Located on the leg · the patient notes enlargement, pain, bothersome appearance and itching · self-categorized by the patient as a rash · a close-up photograph · FST IV · the lesion is described as raised or bumpy · female subject, age 40–49 · associated systemic symptoms include fatigue:
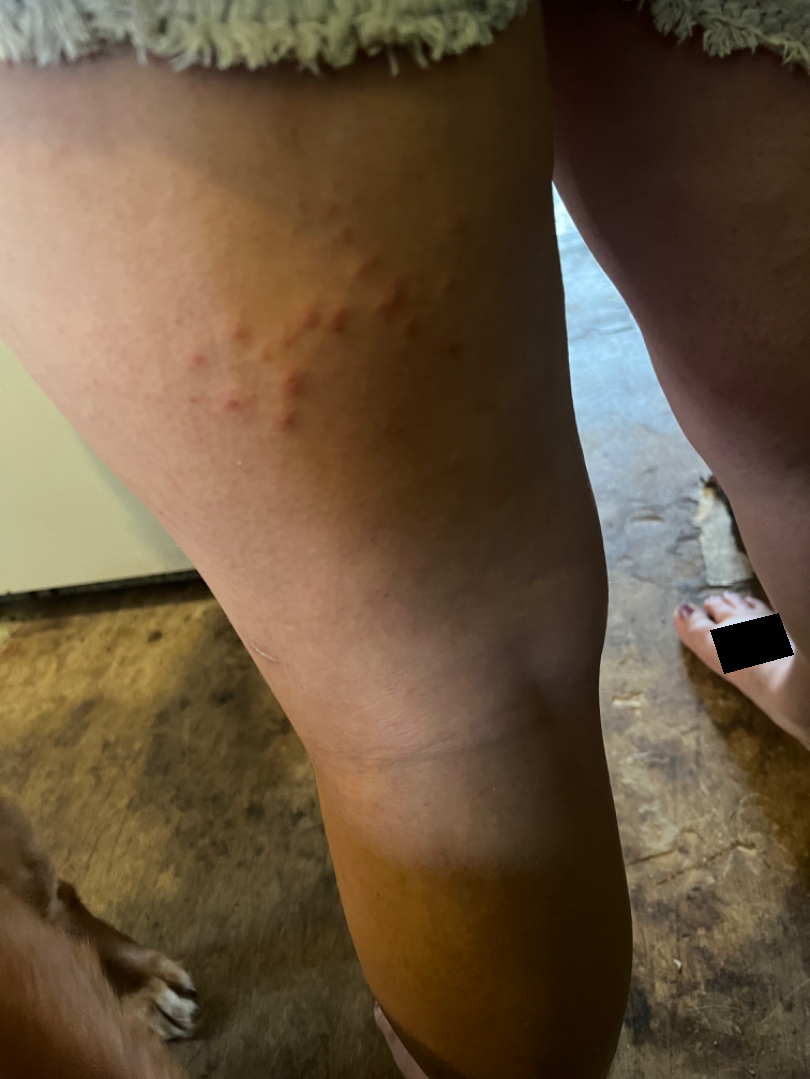  differential:
    tied_lead:
      - Insect Bite
      - Acute dermatitis, NOS